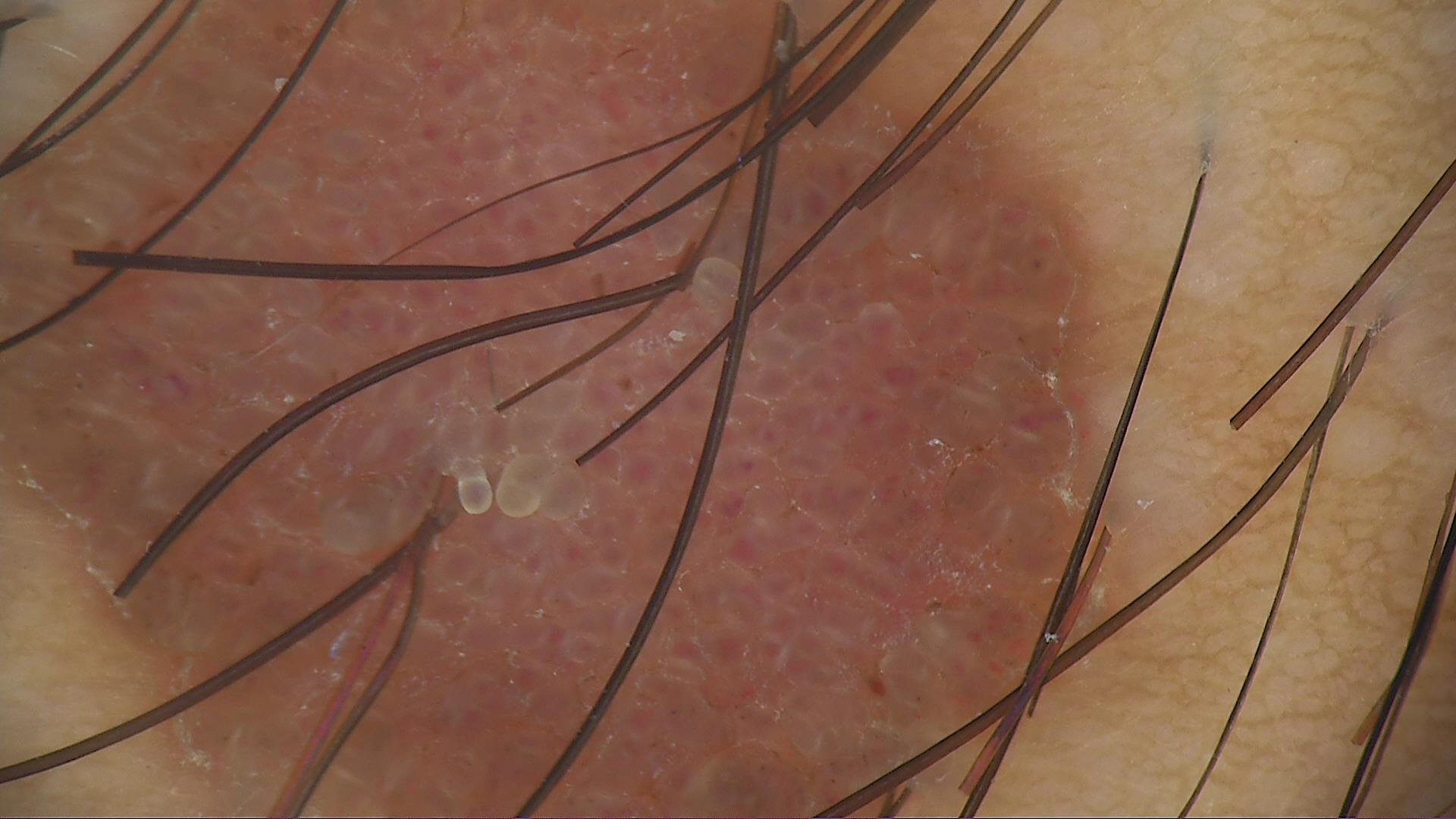A dermoscopic photograph of a skin lesion. The diagnostic label was a banal lesion — a dermal nevus.